A male patient age 77.
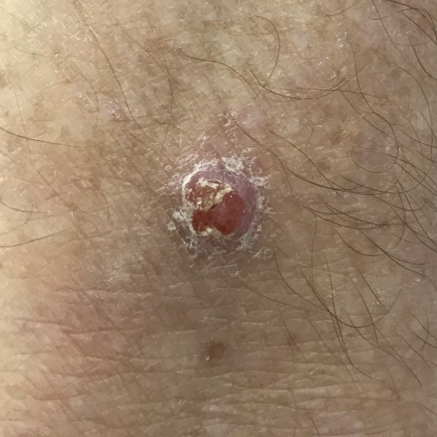The lesion involves a foot. Histopathology confirmed a squamous cell carcinoma.